An image taken at a distance. Female subject, age 50–59:
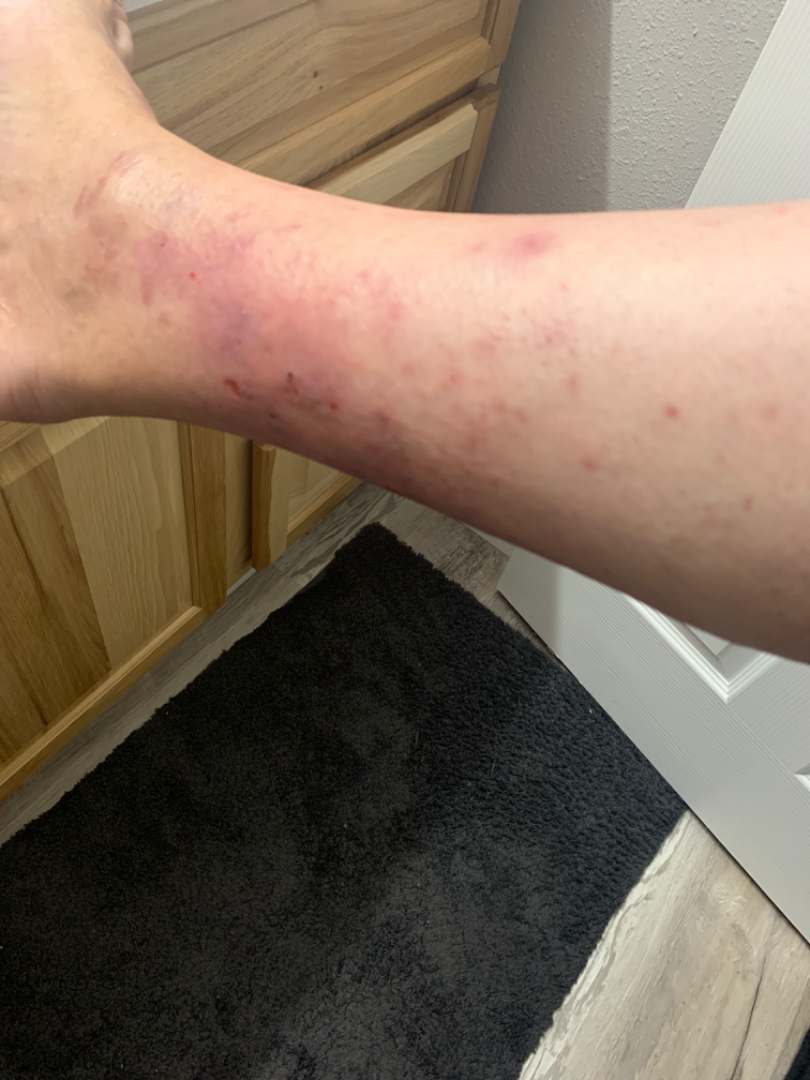Review: The image was not sufficient for the reviewer to characterize the skin condition.